This is a close-up image:
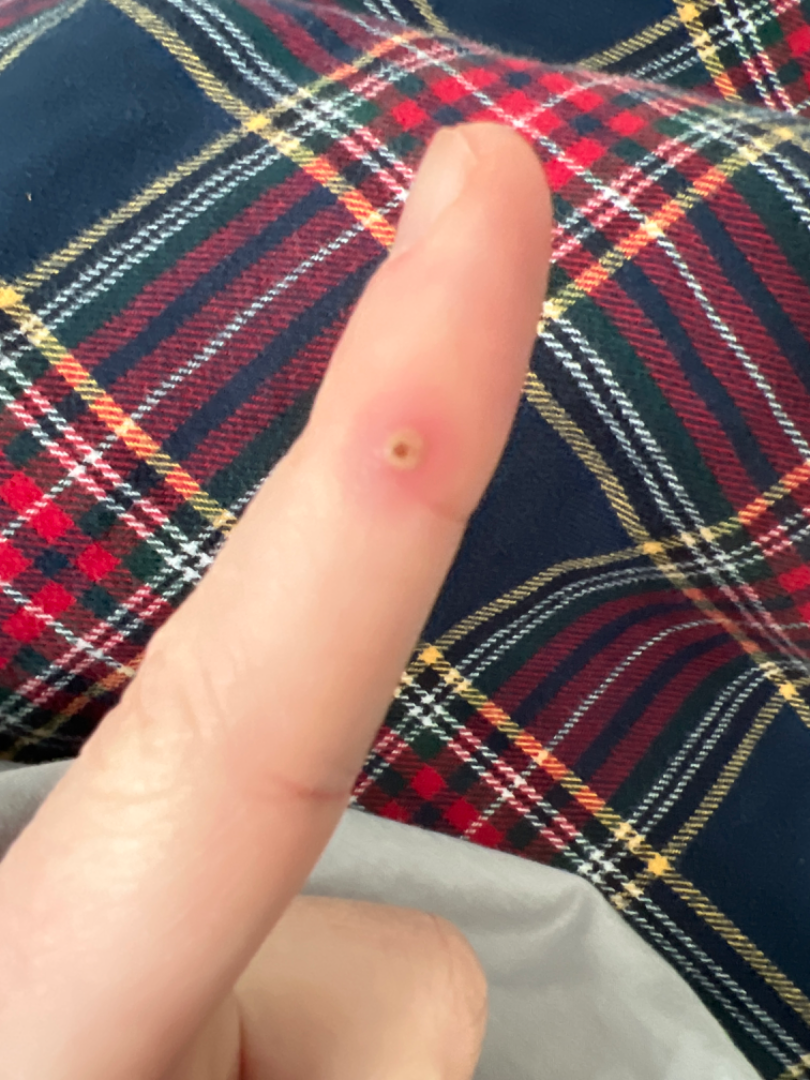Assessment: The dermatologist could not determine a likely condition from the photograph alone.